A clinical photograph showing a skin lesion. By history, alcohol use, prior malignancy (patient or family), and pesticide exposure. A male patient 47 years old:
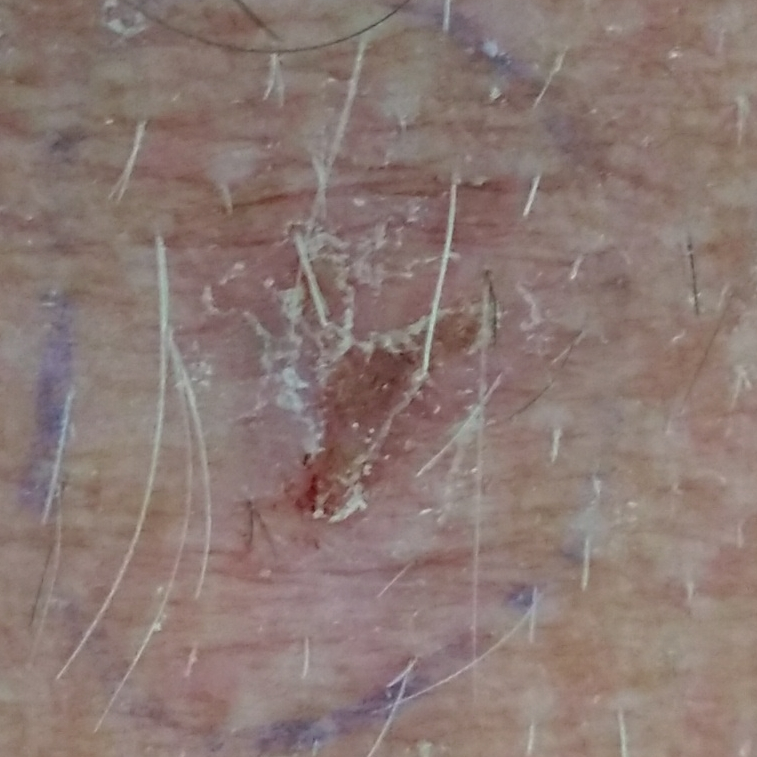The lesion is on the chest. Measuring about 13 × 11 mm. By the patient's account, the lesion has bled, hurts, and itches. Histopathological examination showed a basal cell carcinoma.